Recorded as FST II. A female patient in their mid- to late 80s or older.
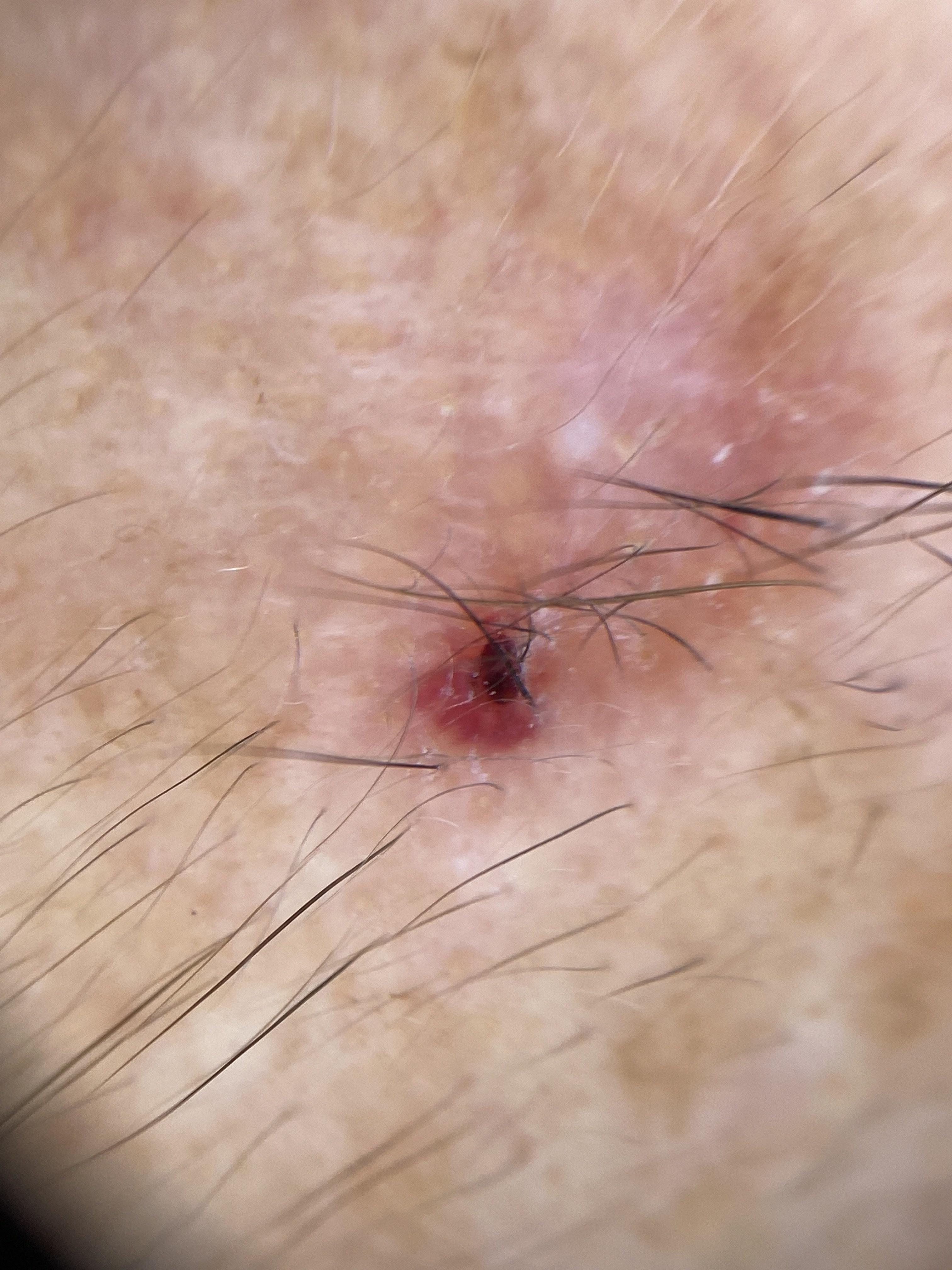On biopsy, the diagnosis was a malignancy — a squamous cell carcinoma.